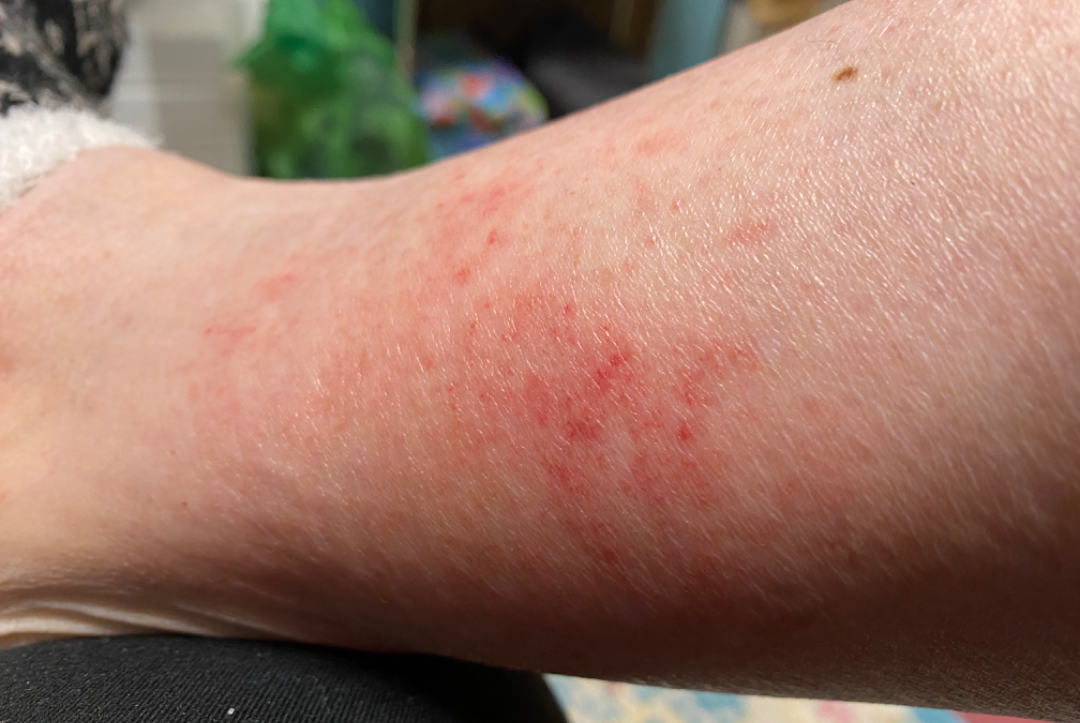Impression:
No differential diagnosis could be assigned on photographic review.
History:
This is a close-up image. The affected area is the leg.